A close-up photograph.
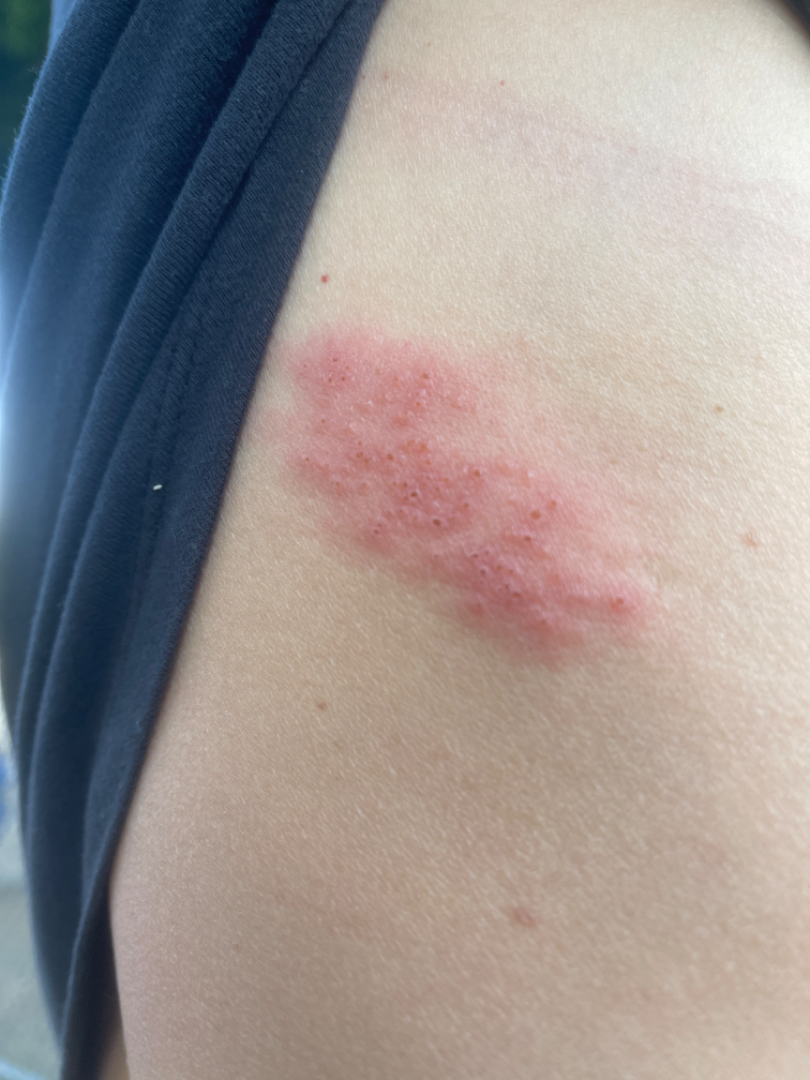  differential:
    leading:
      - Herpes Zoster